A male patient 56 years of age; the patient is Fitzpatrick I:
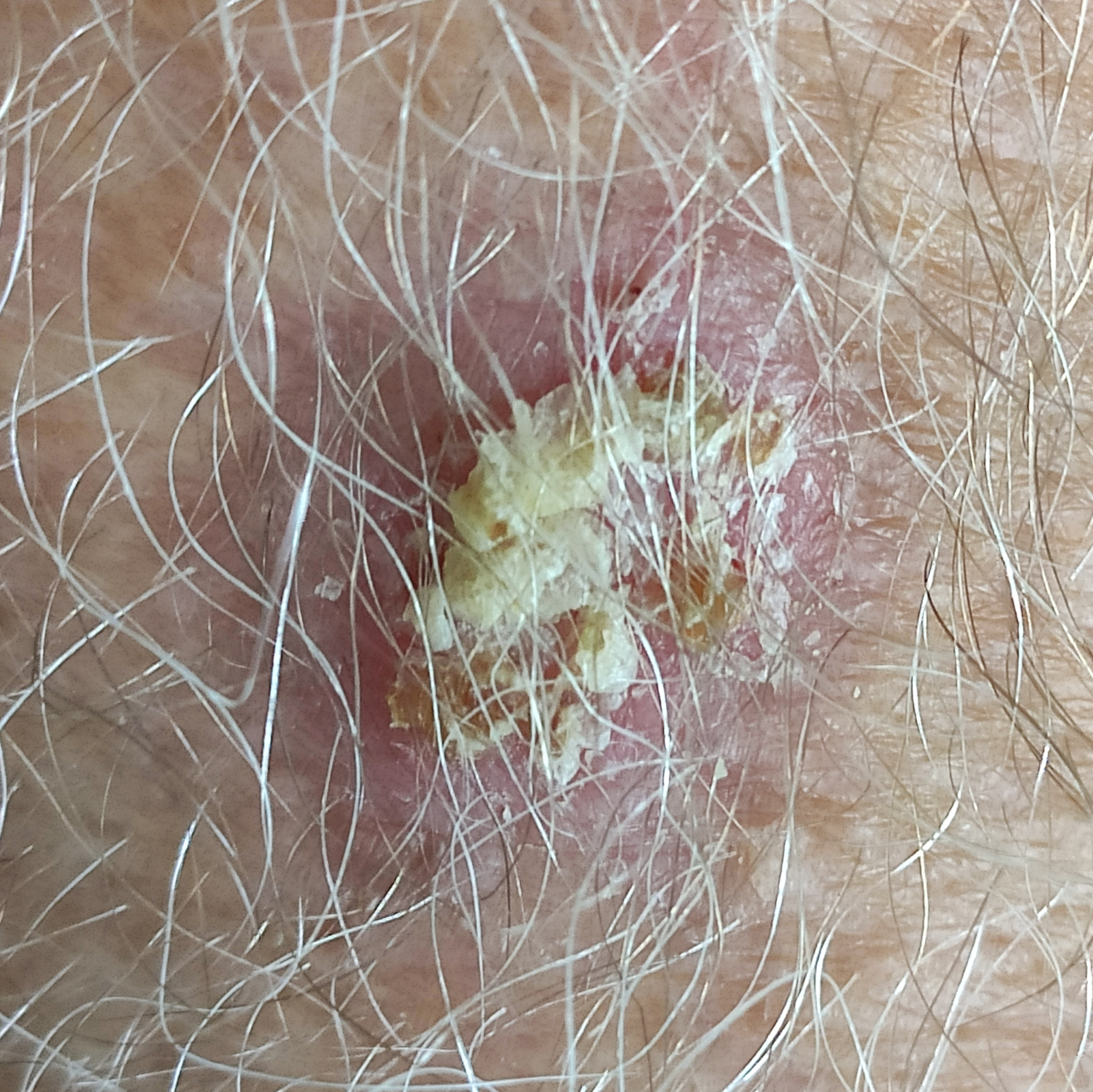Patient and lesion:
The lesion is on a forearm. The lesion is roughly 10 by 10 mm. Per patient report, the lesion is elevated and has changed.
Impression:
Consistent with an actinic keratosis.